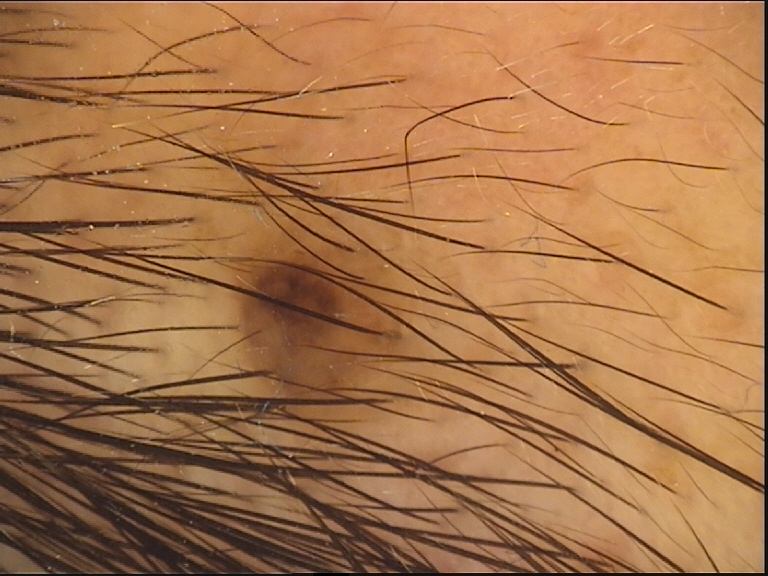{
  "image": "dermoscopy",
  "diagnosis": {
    "name": "dysplastic compound nevus",
    "code": "cd",
    "malignancy": "benign",
    "super_class": "melanocytic",
    "confirmation": "expert consensus"
  }
}